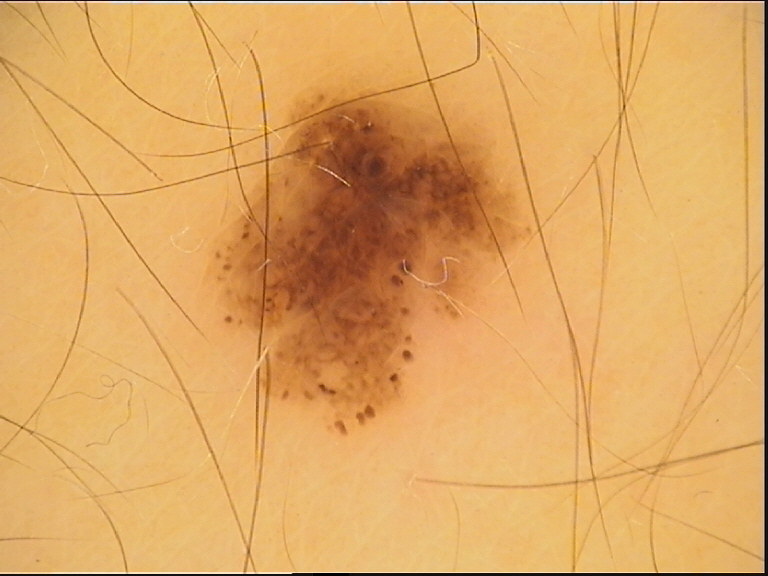modality — dermatoscopy | class — dysplastic junctional nevus (expert consensus).